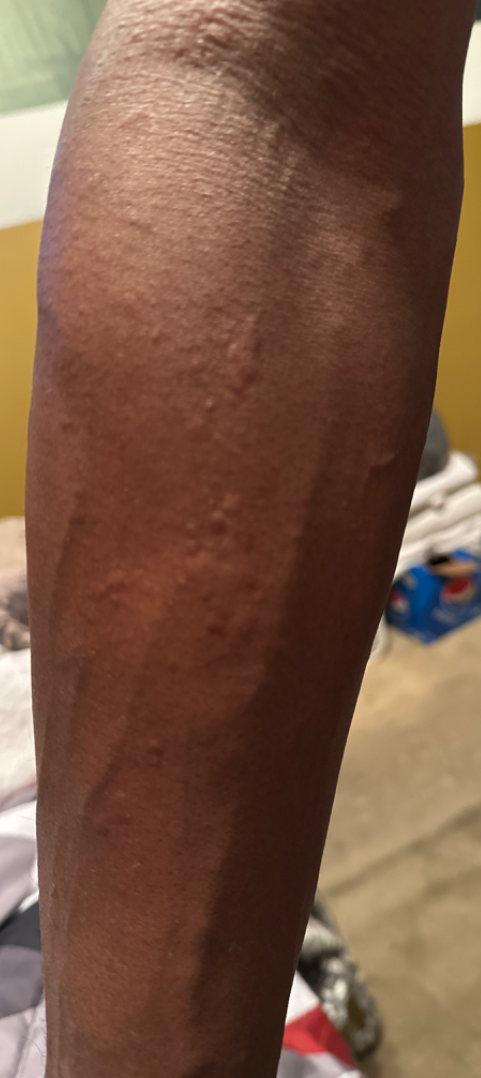The case was difficult to assess from the available photograph. The affected area is the leg, arm and front of the torso. Reported lesion symptoms include itching. The photograph was taken at a distance. The patient reported no systemic symptoms.